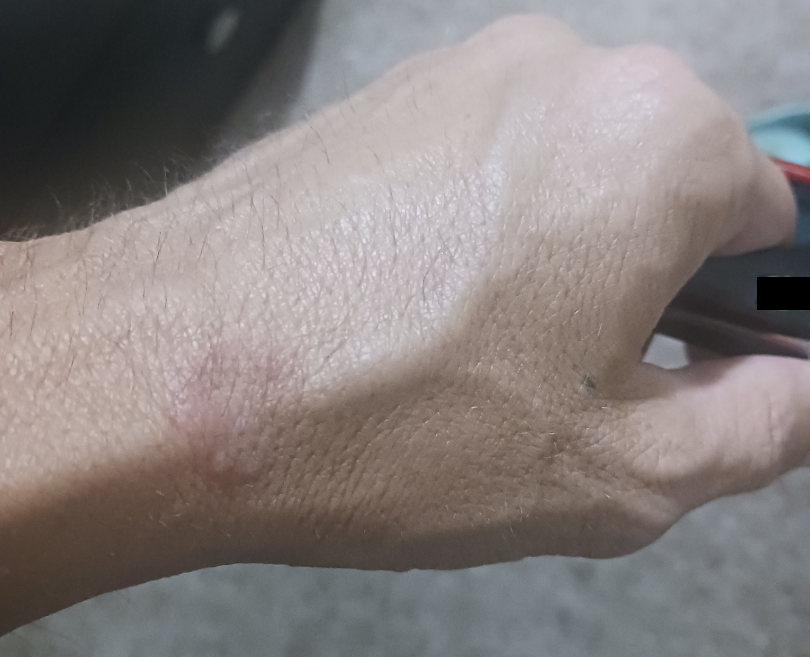The condition has been present for about one day.
The patient reported no systemic symptoms.
Texture is reported as fluid-filled and raised or bumpy.
The patient is a male aged 30–39.
Lay graders estimated Monk Skin Tone 2 (US pool) or 3 (India pool).
Symptoms reported: itching.
An image taken at an angle.
On photographic review by a dermatologist, most consistent with Granuloma annulare.